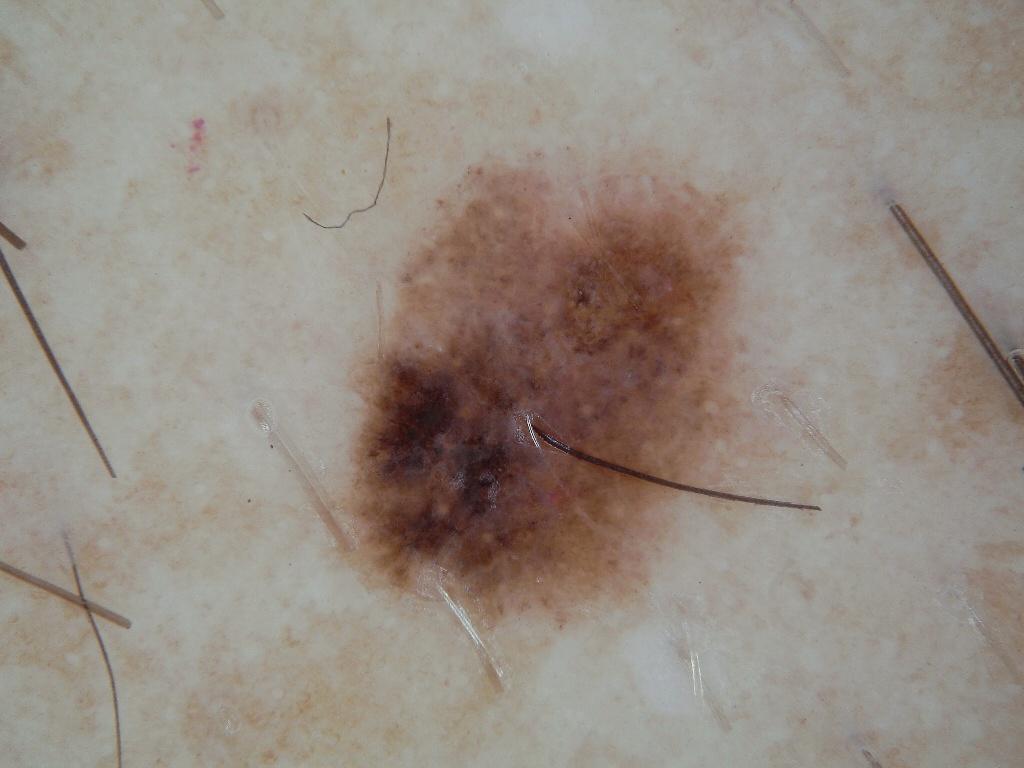image:
  modality: dermoscopy
lesion_location:
  bbox_xyxy:
    - 320
    - 165
    - 759
    - 629
lesion_extent:
  approx_field_fraction_pct: 19
dermoscopic_features:
  present: []
  absent:
    - streaks
    - globules
diagnosis:
  malignancy: benign
  provenance: clinical